Collected as part of a research study, without a referral diagnosis · the patient says their skin tans without first burning · a skin lesion imaged with a dermatoscope · a female patient age 60 · few moles overall by the patient's own estimate: 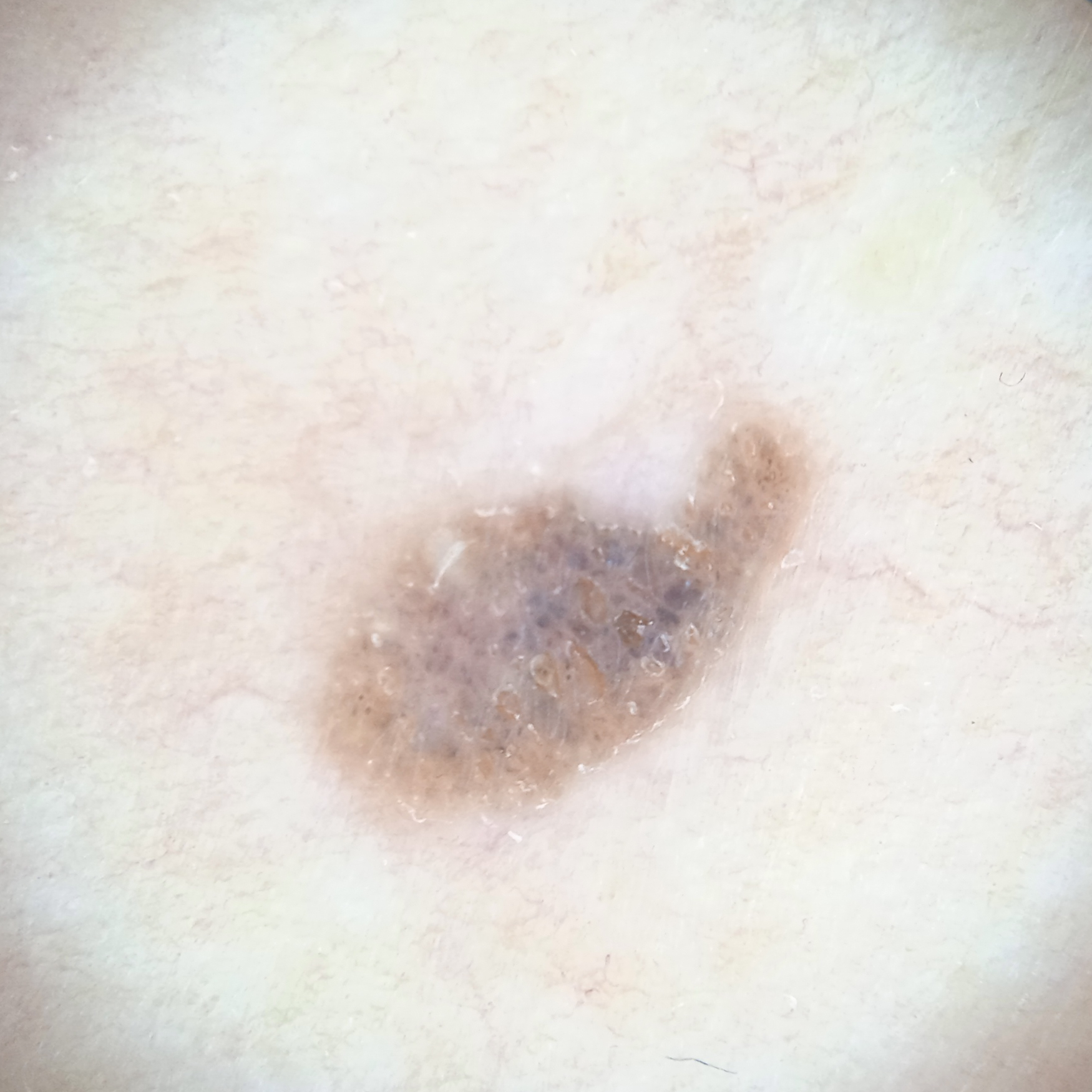Q: What is the anatomic site?
A: the torso
Q: How large is the lesion?
A: 6.2 mm
Q: What was the diagnosis?
A: seborrheic keratosis (dermatologist consensus)